The patient says their skin reddens with sun exposure · a clinical photograph showing a skin lesion · imaged for a research study, with no referral diagnosis recorded · a moderate number of moles by the patient's own estimate · a female patient age 27: 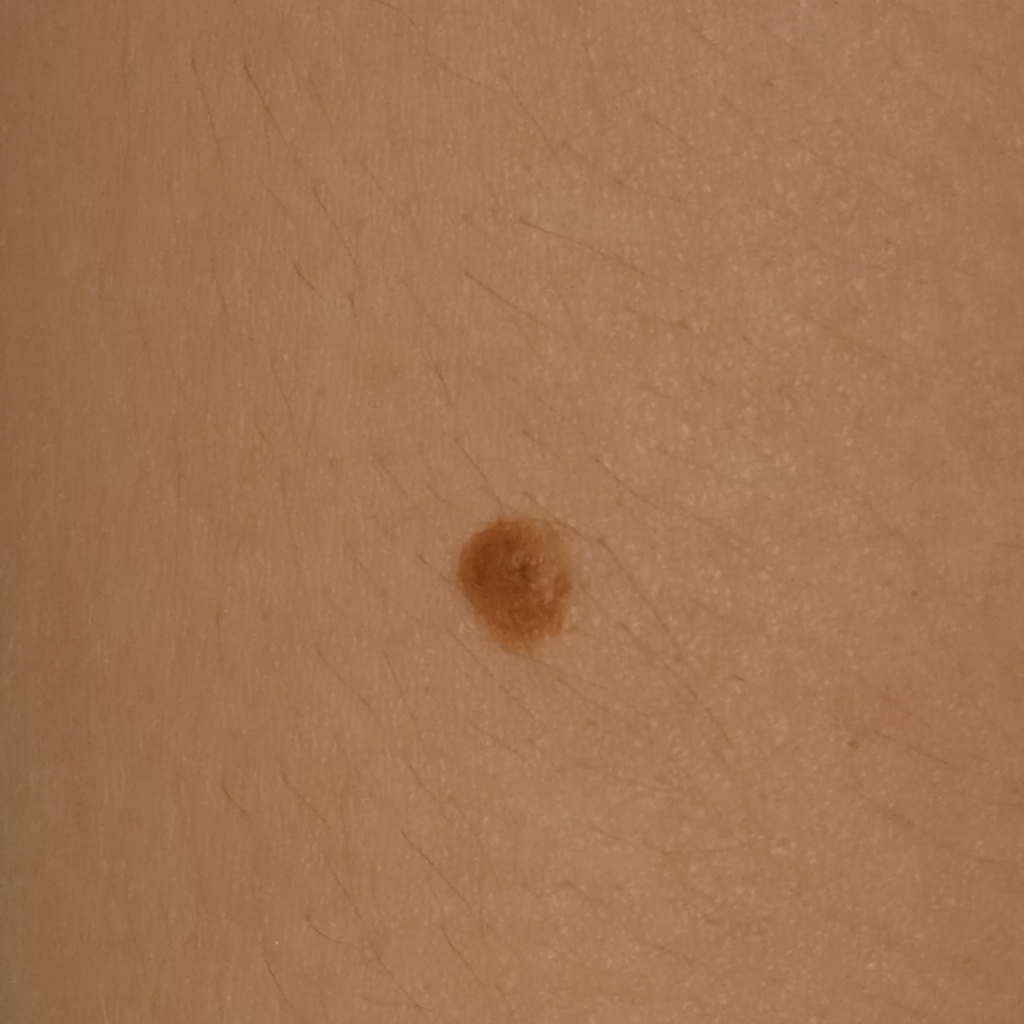| field | value |
|---|---|
| site | the torso |
| lesion size | 4.4 mm |
| diagnostic label | melanocytic nevus (dermatologist consensus) |